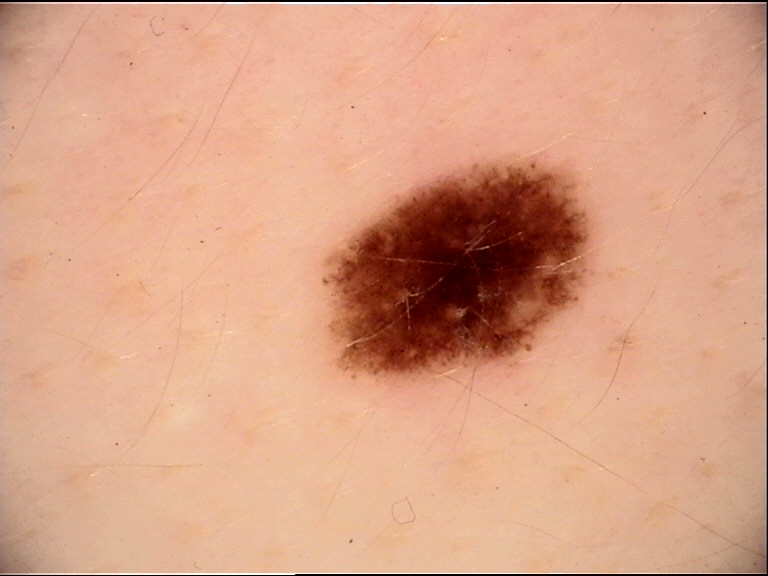Impression: Classified as a dysplastic junctional nevus.